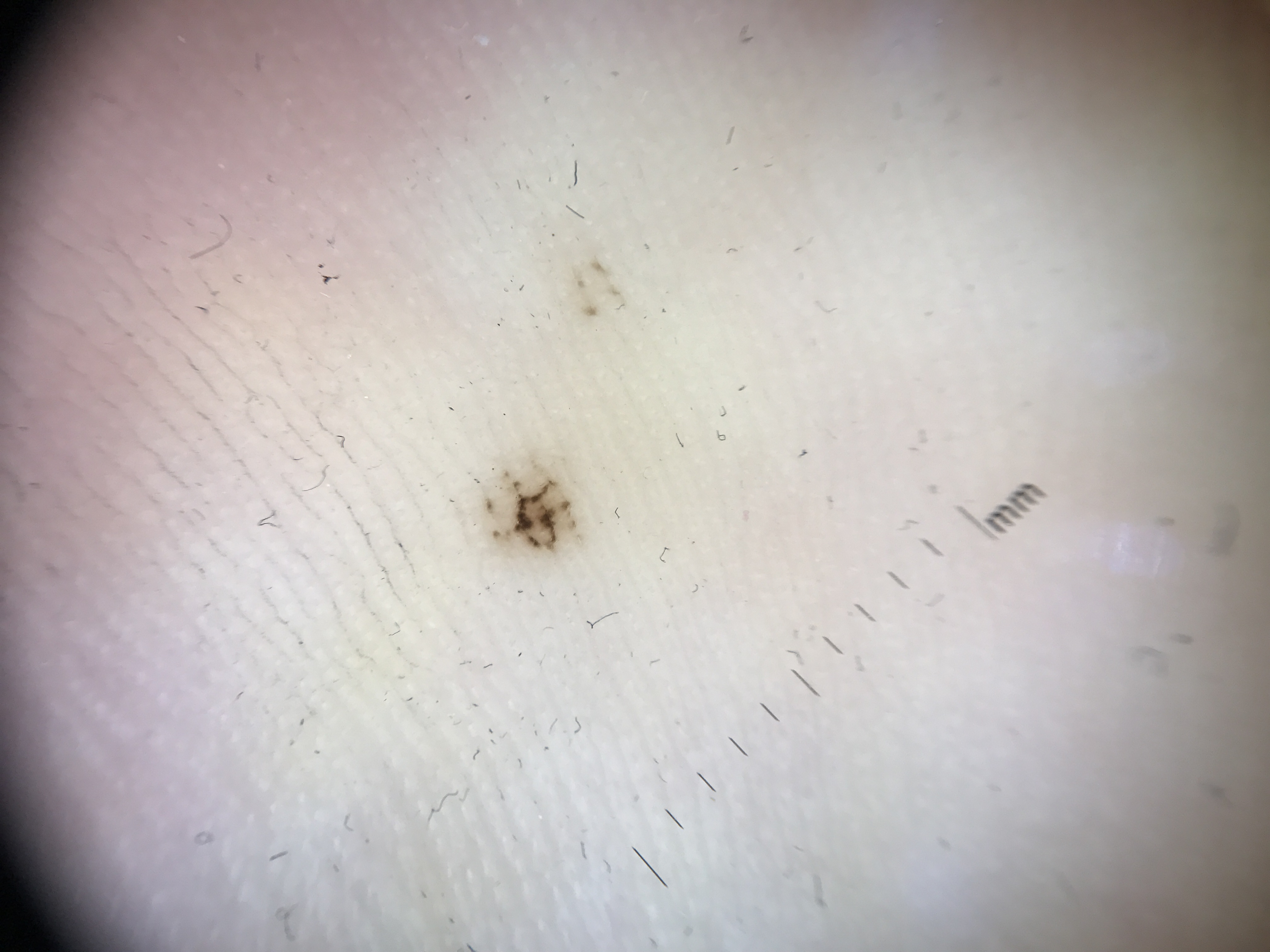Q: What is the imaging modality?
A: dermatoscopy
Q: What is this lesion?
A: acral junctional nevus (expert consensus)